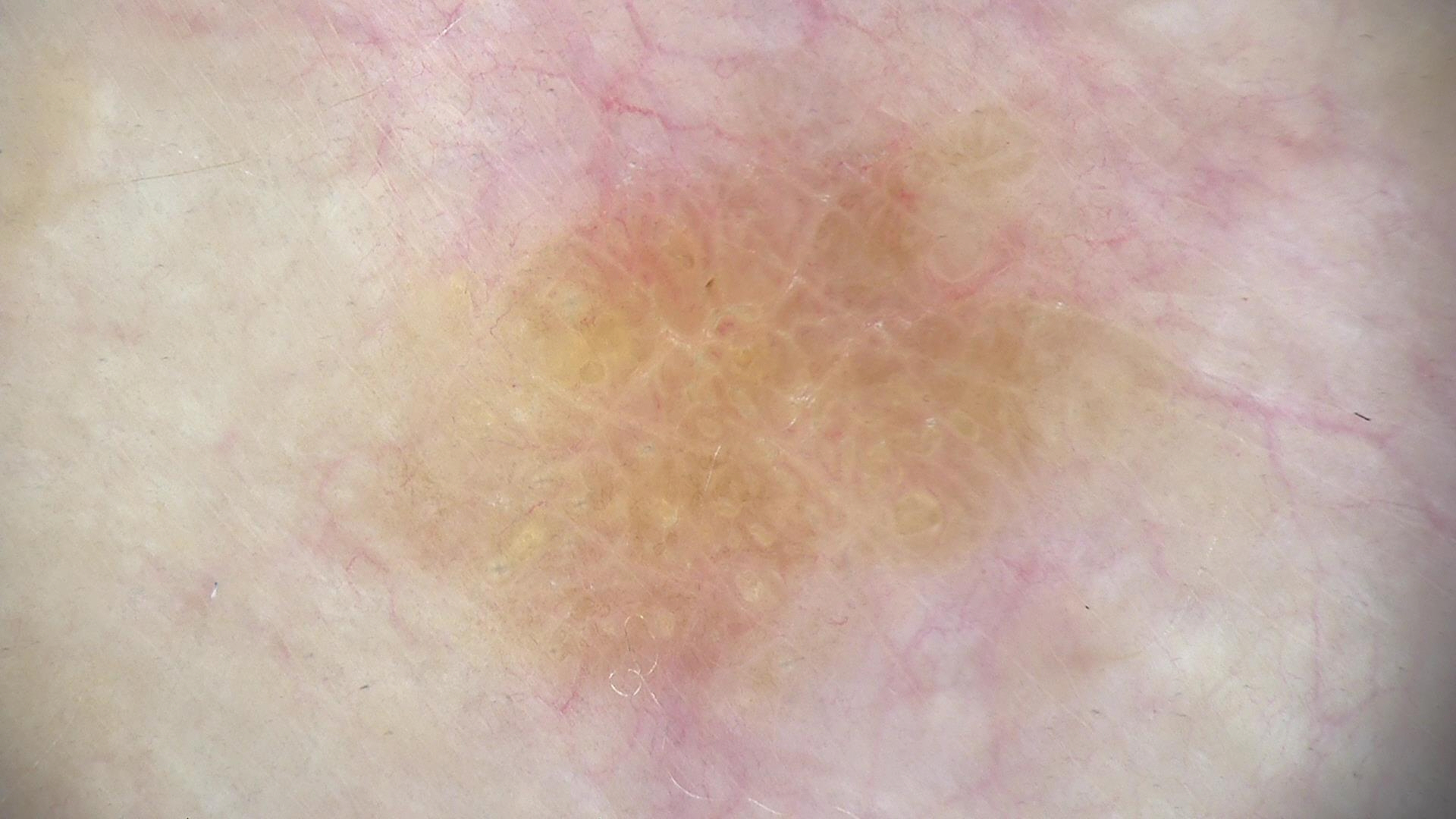Findings:
- class · seborrheic keratosis (expert consensus)